Symptoms reported: itching and burning · no associated systemic symptoms reported · texture is reported as raised or bumpy · female contributor, age 30–39 · the photograph is a close-up of the affected area · present for less than one week · self-categorized by the patient as a rash.
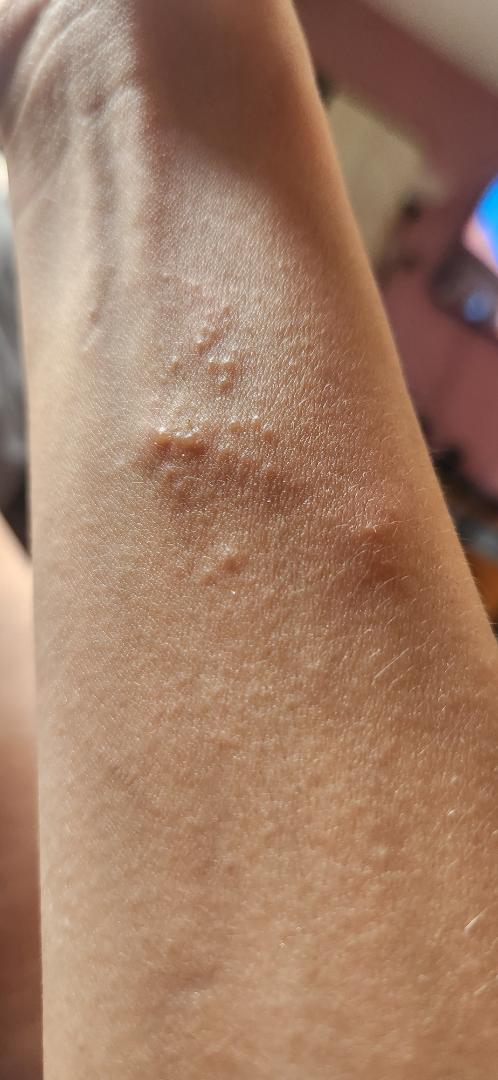On photographic review: most consistent with Koebner phenomenon.